A dermatoscopic image of a skin lesion.
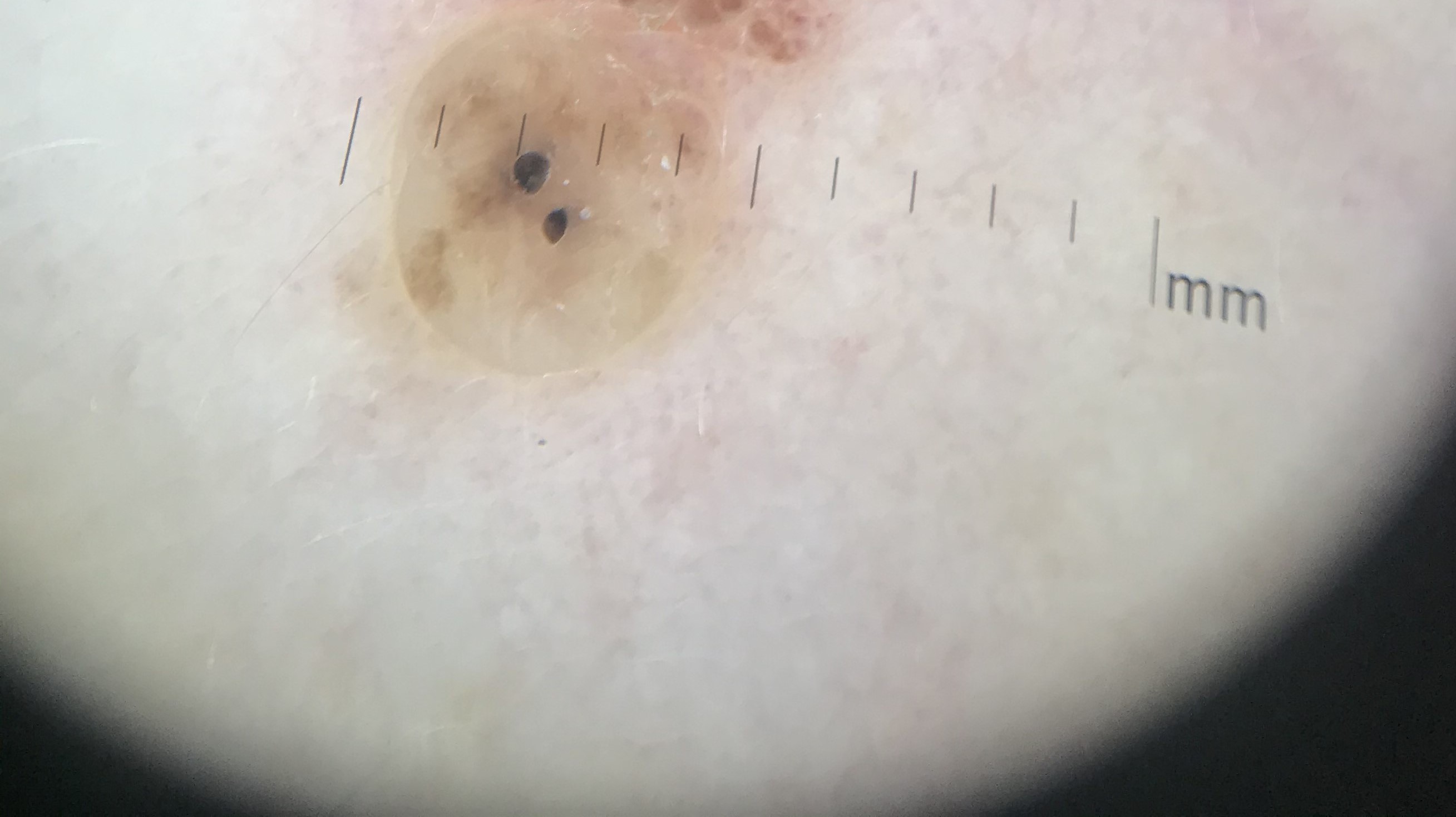The morphology is that of a banal lesion. Consistent with a dermal nevus.